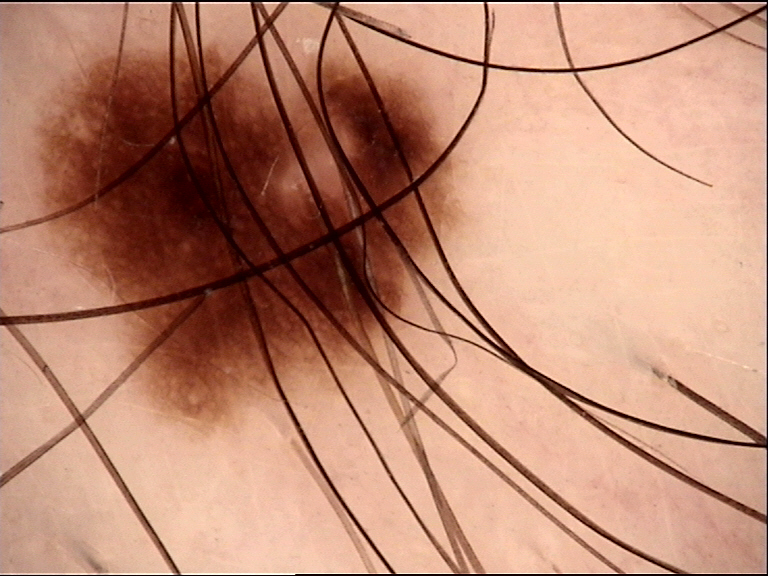Findings:
A dermatoscopic image of a skin lesion.
Conclusion:
The diagnosis was a junctional nevus.